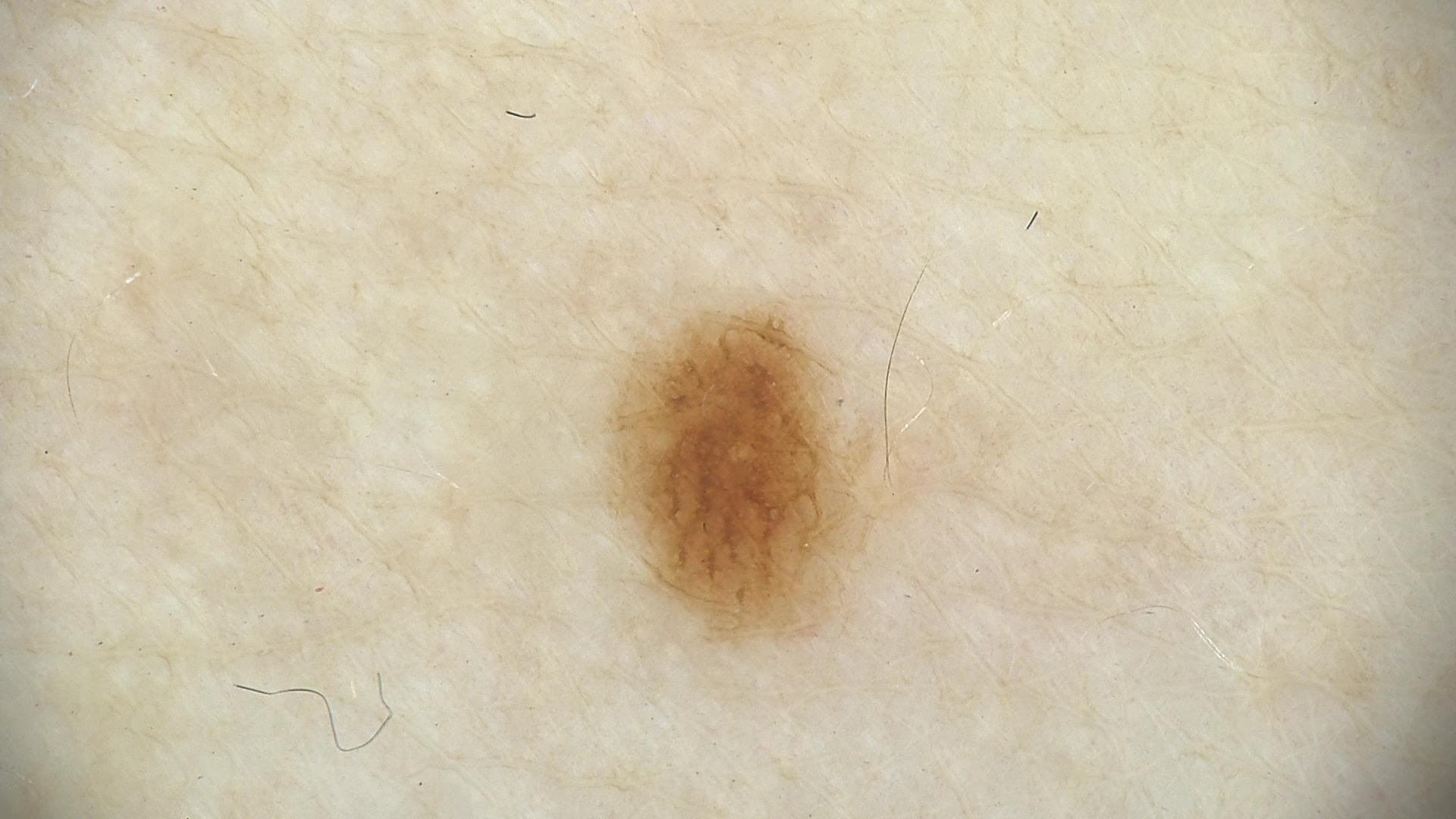Summary: A dermatoscopic image of a skin lesion. Conclusion: Diagnosed as a dysplastic junctional nevus.